A dermoscopy image of a single skin lesion:
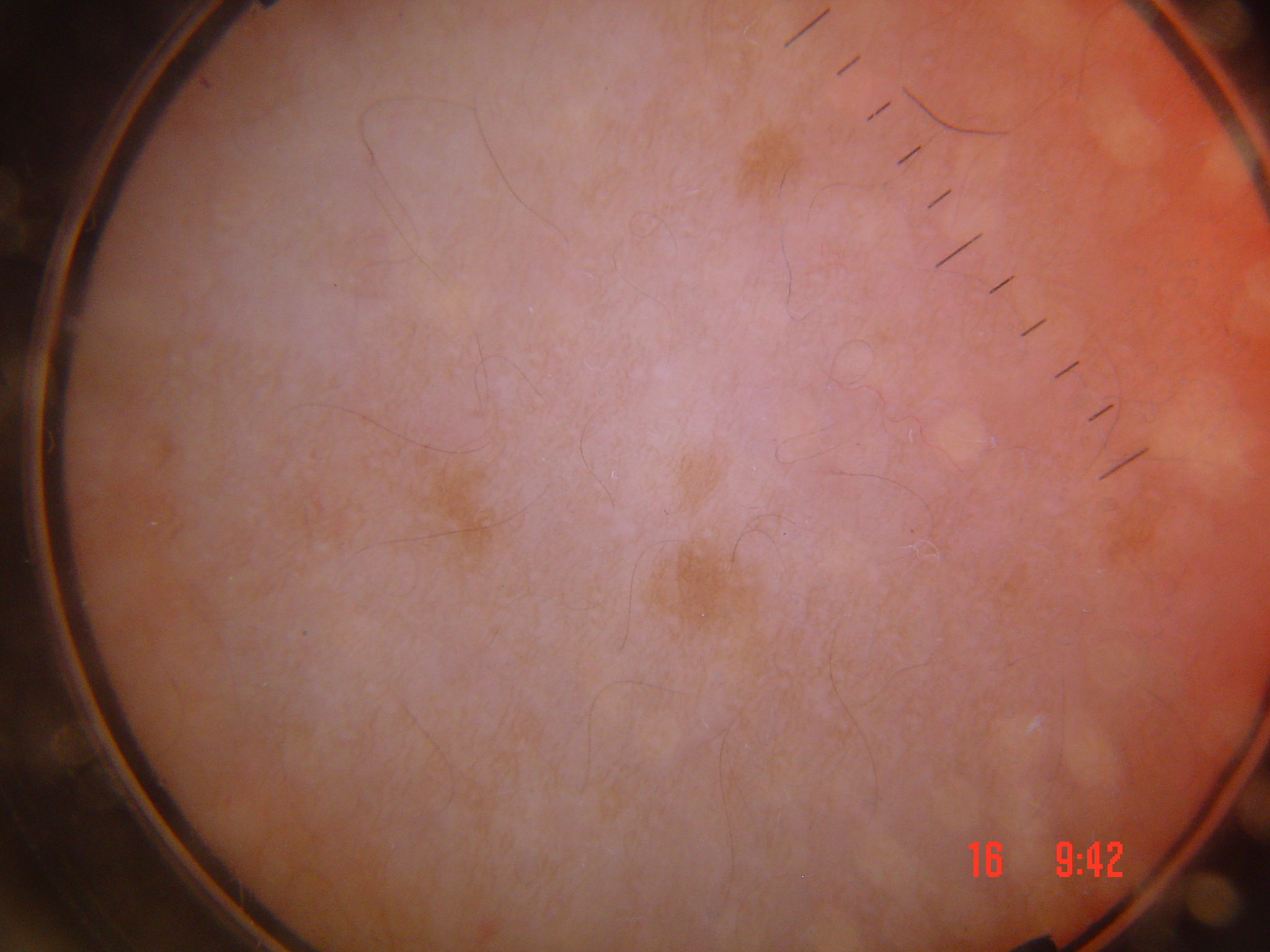Q: What is the diagnosis?
A: lentigo simplex (expert consensus)